Reported lesion symptoms include bothersome appearance, pain, darkening and enlargement. The patient described the issue as a rash. The condition has been present for one to four weeks. The lesion involves the front of the torso and back of the torso. The photograph is a close-up of the affected area.
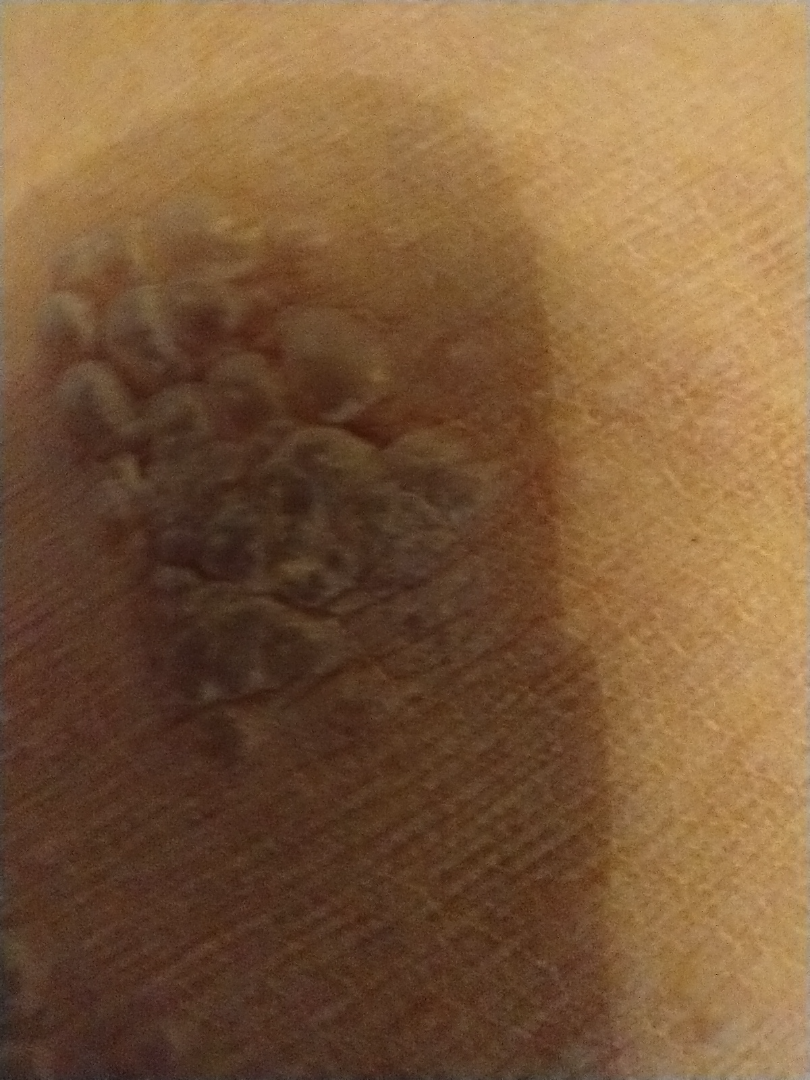Assessment: The skin findings could not be characterized from the image.